Dermoscopy of a skin lesion.
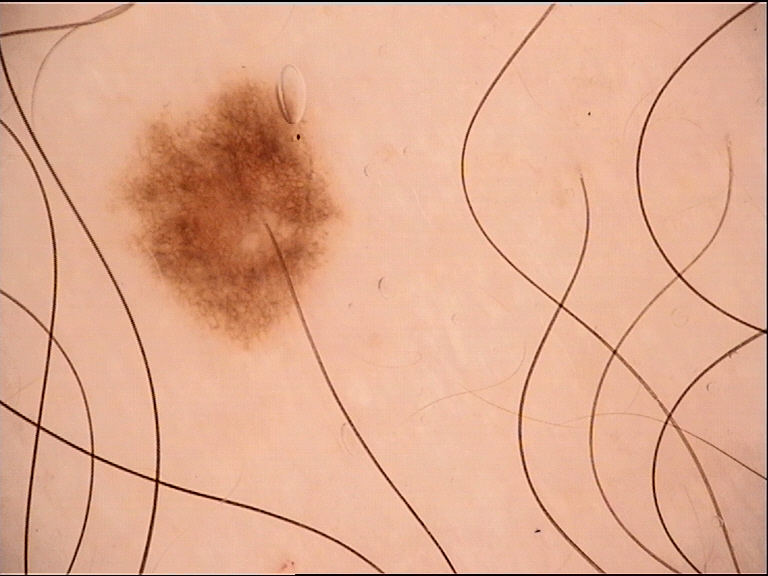Conclusion:
Labeled as a benign lesion — a dysplastic junctional nevus.